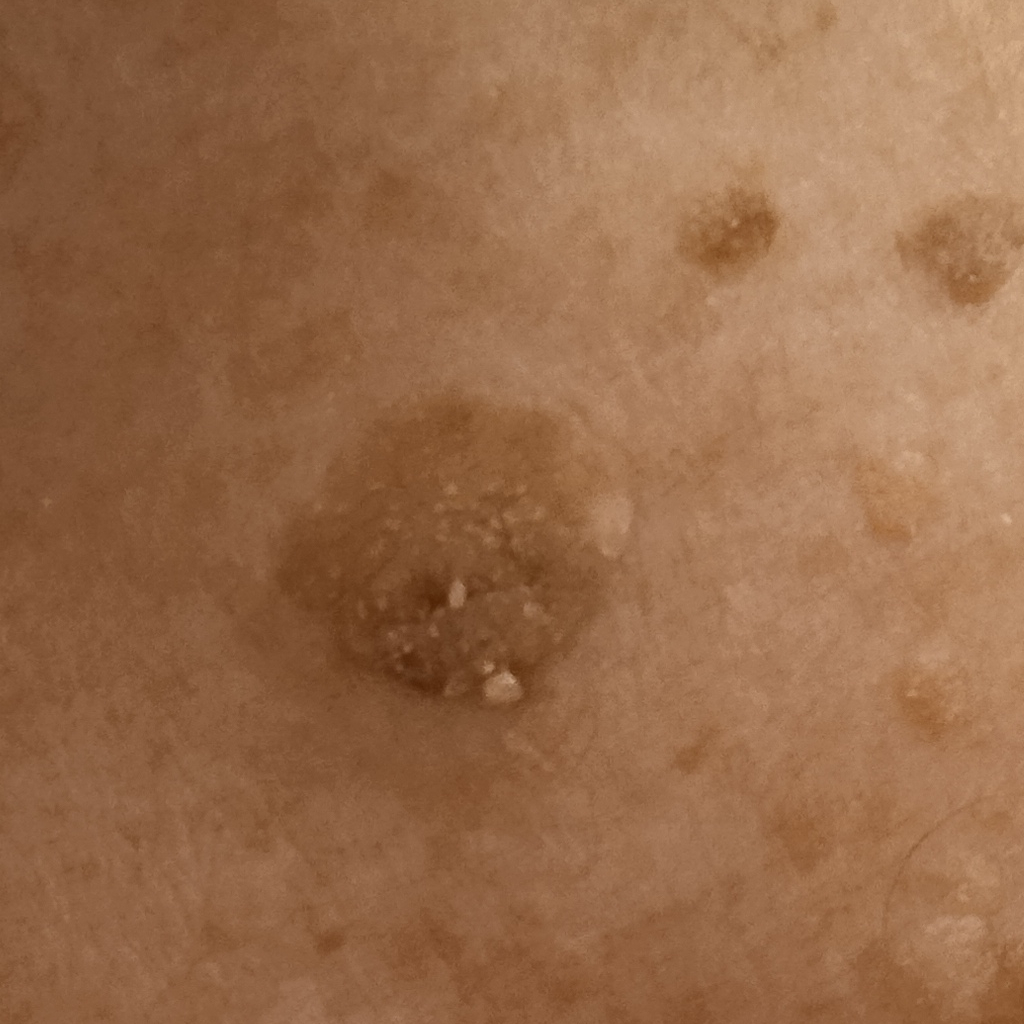diagnostic label = seborrheic keratosis (dermatologist consensus).